Few moles overall by the patient's own estimate; the patient says their skin reddens with sun exposure; imaged for a research study, with no referral diagnosis recorded; on a questionnaire the patient reported a personal history of cancer and a personal history of skin cancer; a macroscopic clinical photograph of a skin lesion; a female subject age 71: 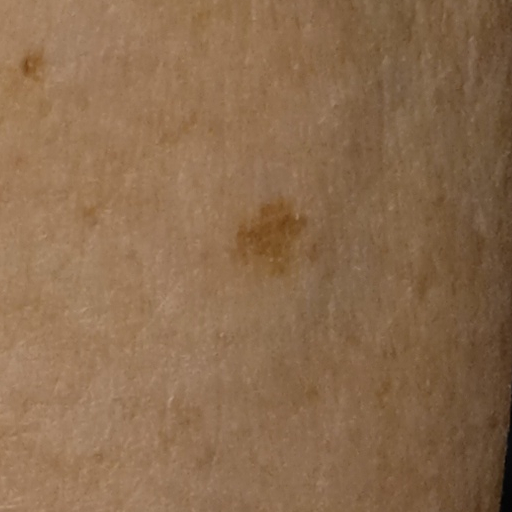The lesion is on an arm.
Measuring roughly 6.1 mm.
The dermatologists' assessment was a melanocytic nevus.